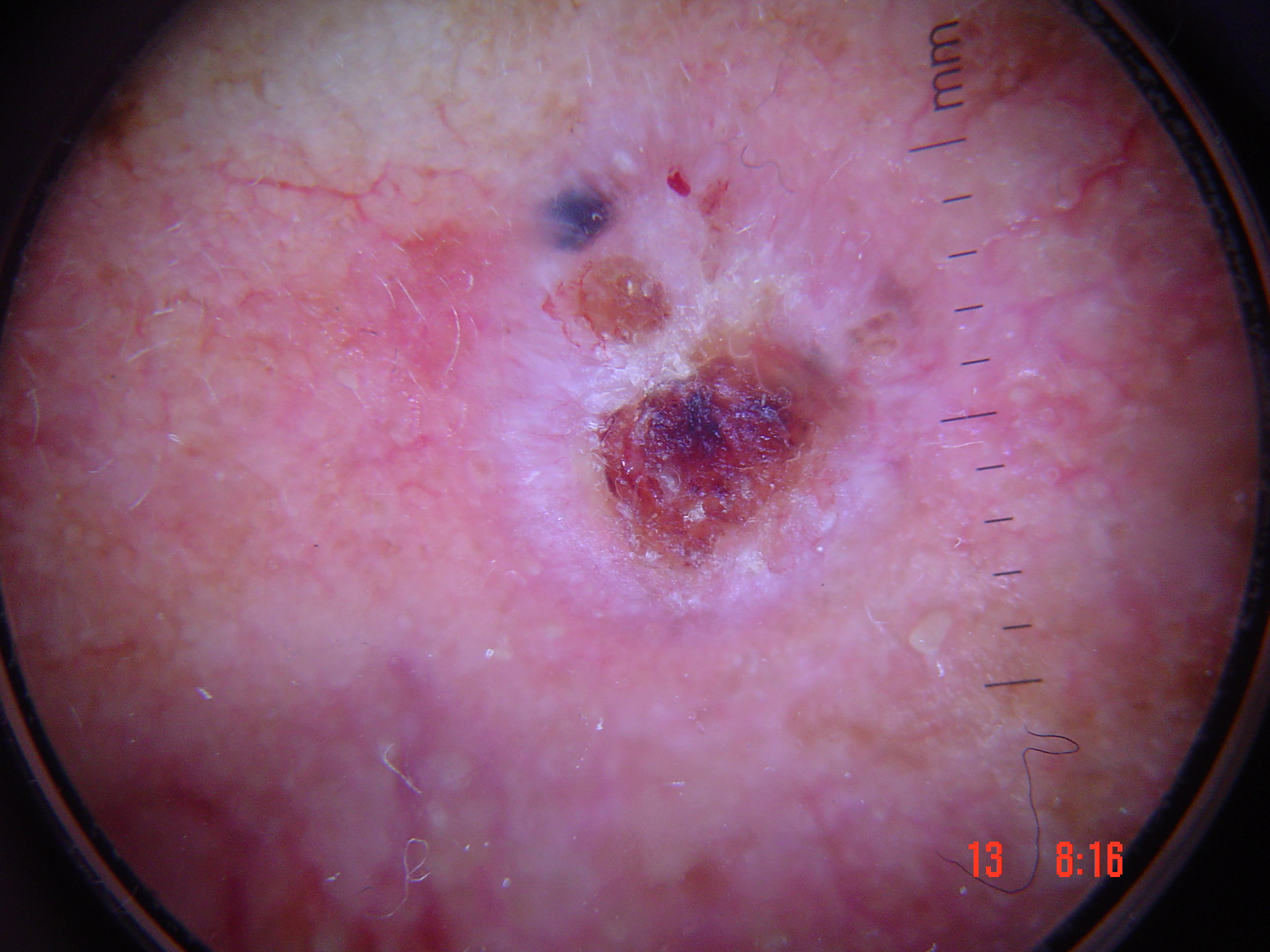Biopsy-confirmed as a basal cell carcinoma.